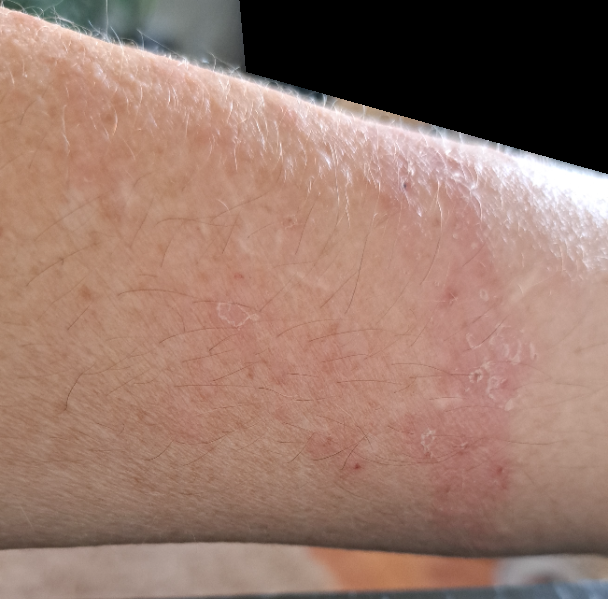Findings:
– image framing: at an angle
– body site: arm
– subject: female, age 60–69
– clinical impression: Allergic Contact Dermatitis and Irritant Contact Dermatitis were considered with similar weight